The patient says their skin tans without first burning. The patient reports no personal history of cancer. The patient describes having few moles overall: 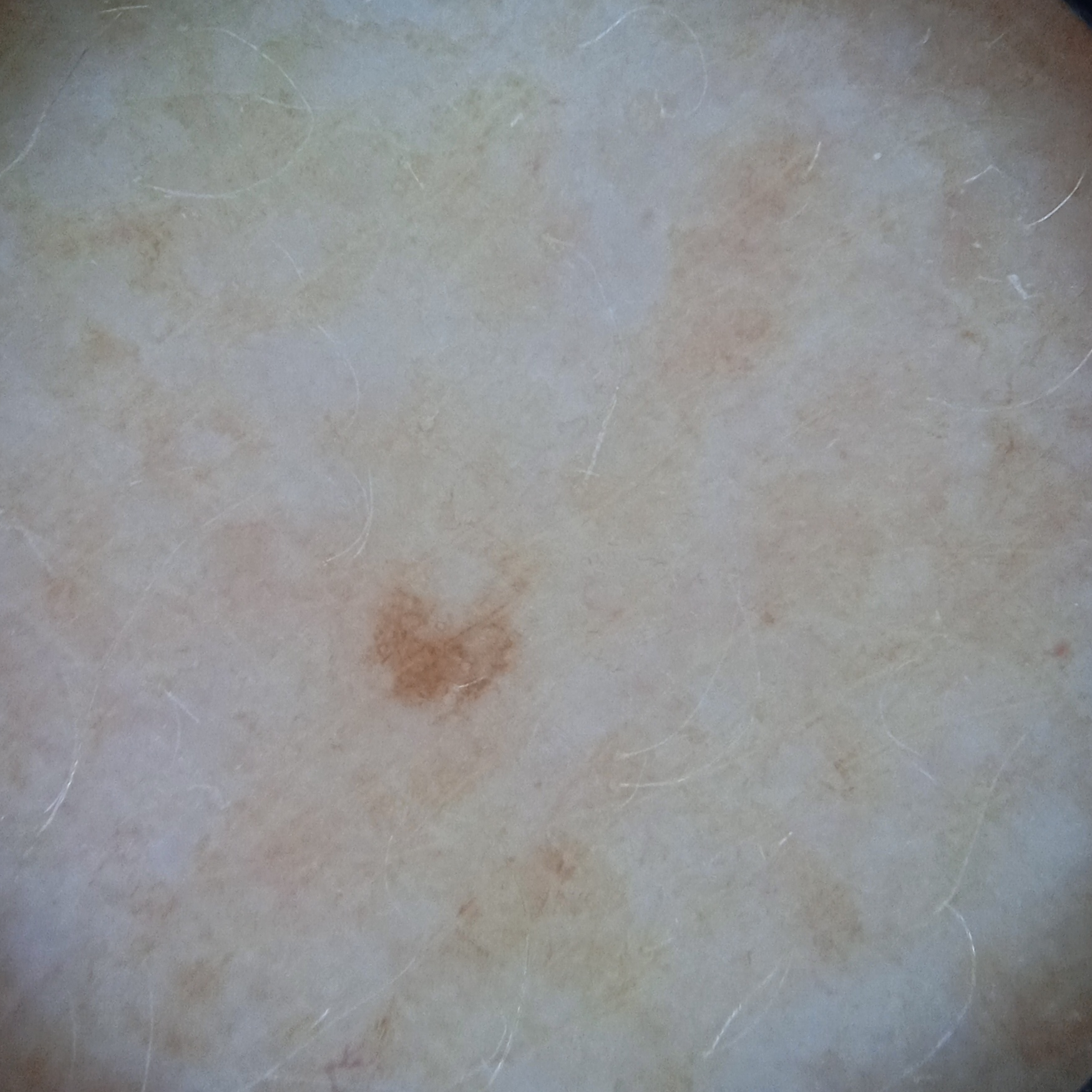  diagnosis:
    name: melanocytic nevus
    malignancy: benign